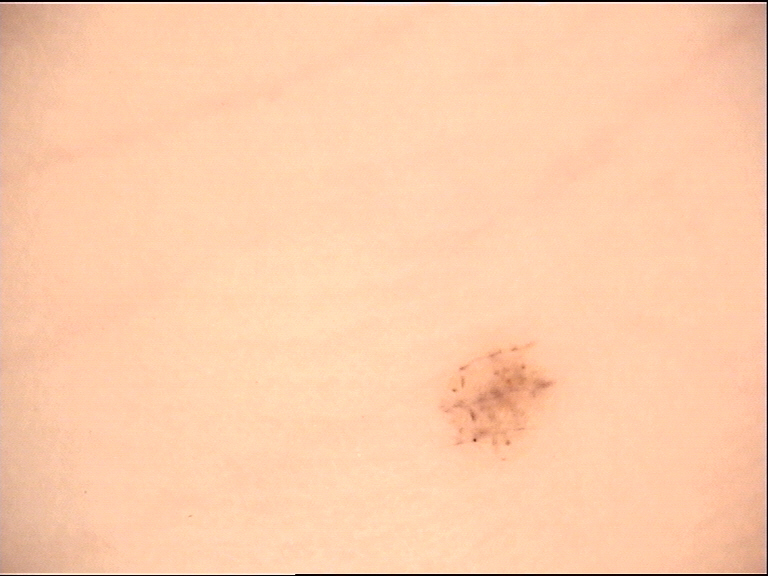Consistent with an acral dysplastic junctional nevus.